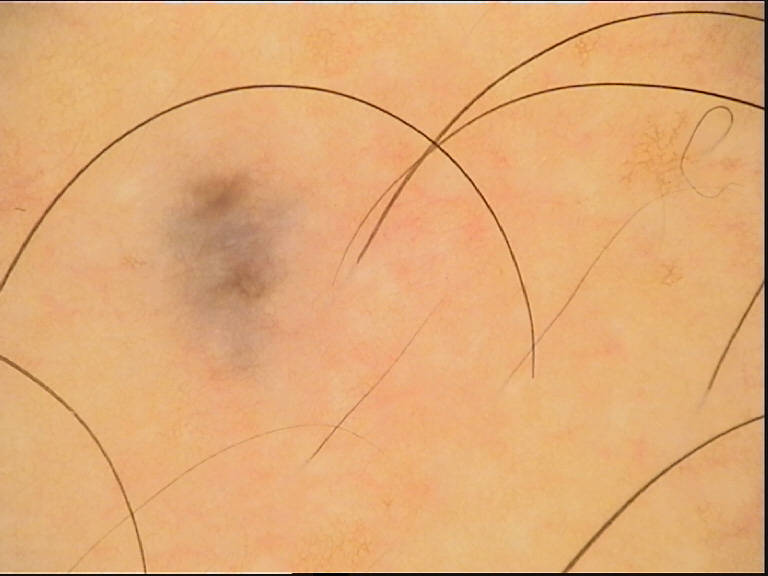Summary: A dermoscopy image of a single skin lesion. The morphology is that of a dermal, banal lesion. Impression: The diagnostic label was a blue nevus.